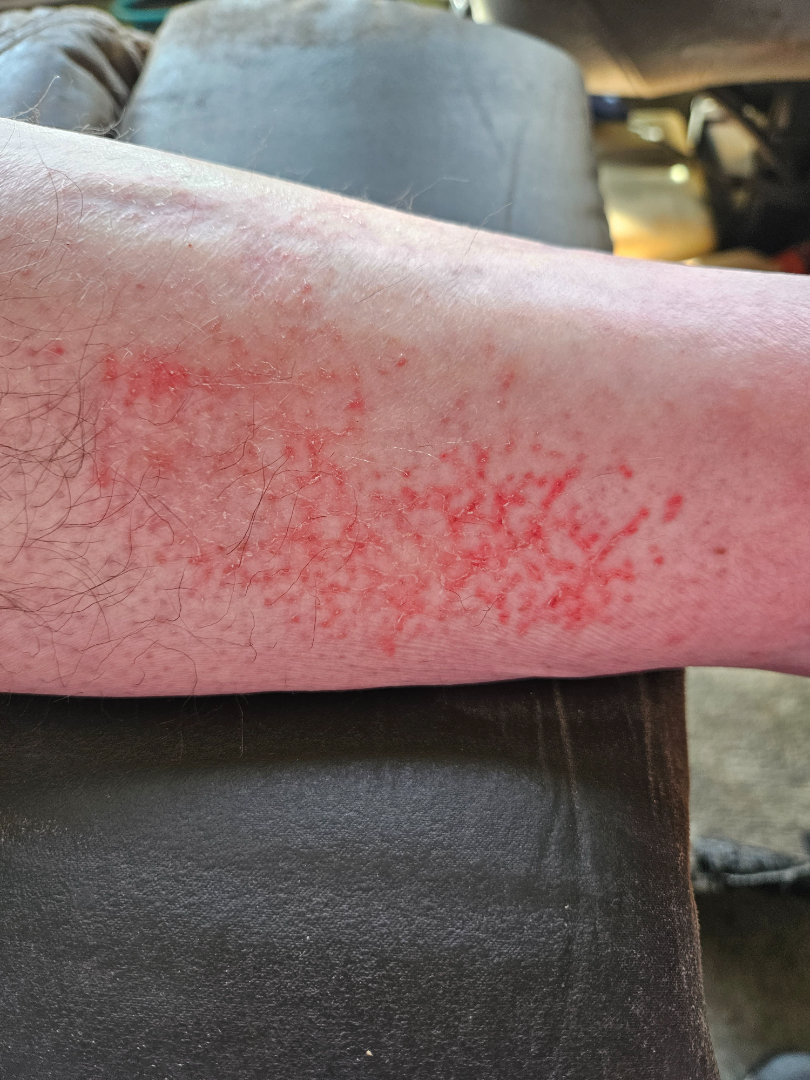Findings:
– clinical impression: consistent with Eczema